Close-up view; female contributor, age 30–39; the affected area is the arm and leg — 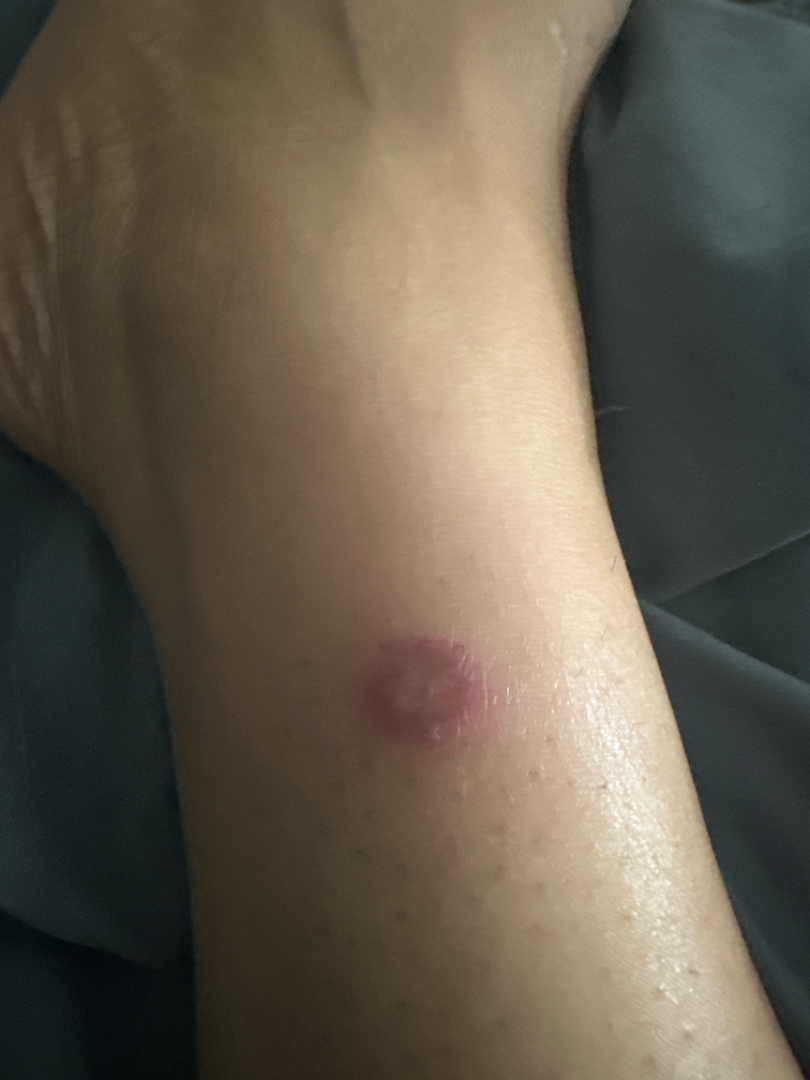patient-reported symptoms: burning and itching
history: more than one year
skin tone: Fitzpatrick IV; lay graders estimated 3 on the Monk skin tone scale
differential diagnosis: Scar Condition, Granuloma annulare and Basal Cell Carcinoma were each considered, in no particular order